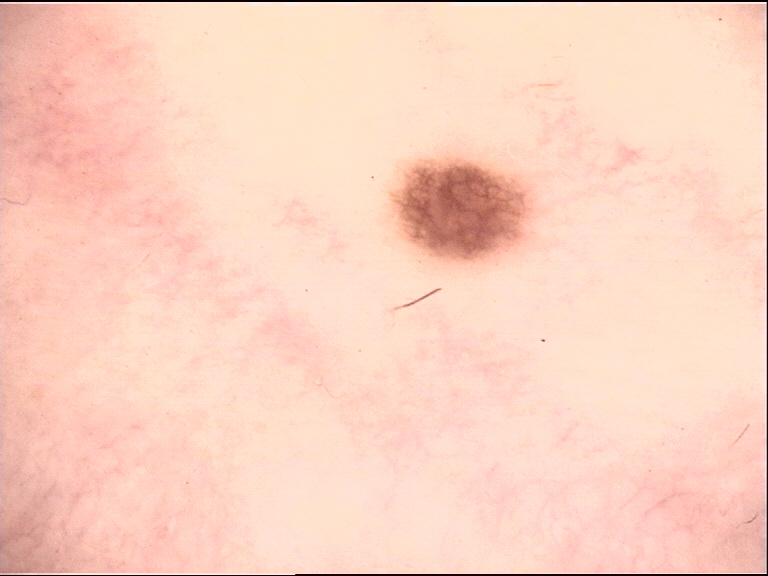image: dermoscopy; class: dysplastic junctional nevus (expert consensus).